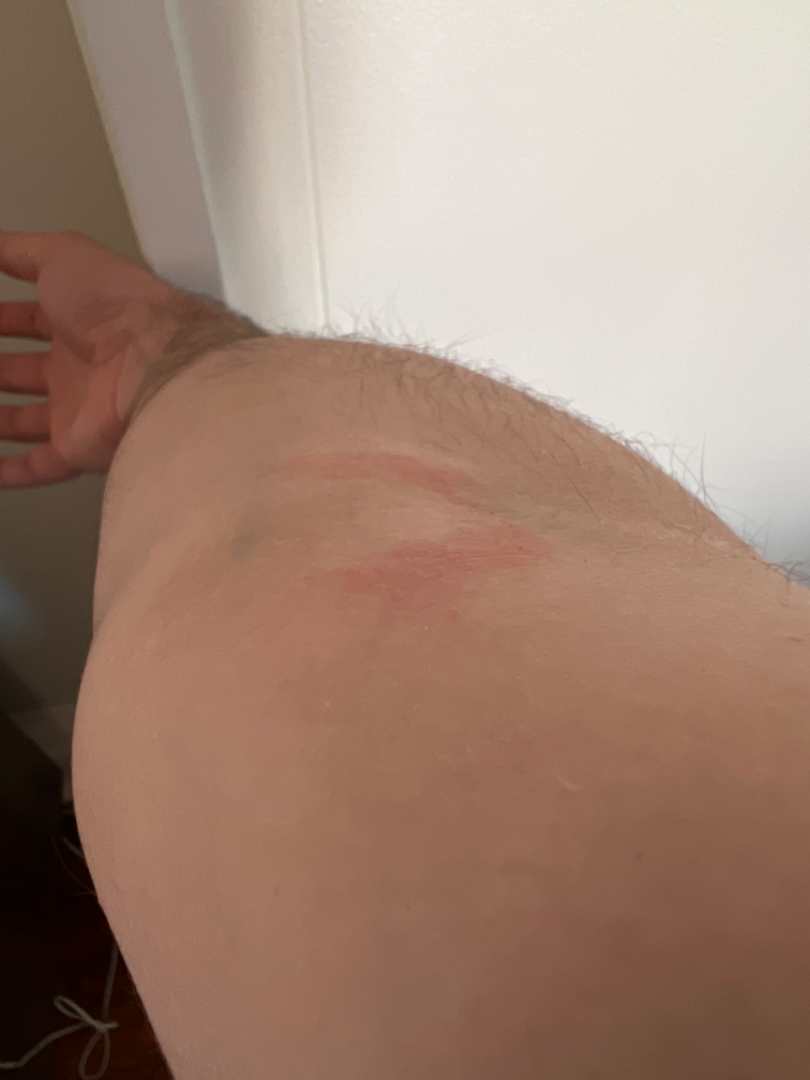Review: The dermatologist could not determine a likely condition from the photograph alone.